The patient describes having numerous moles · a clinical photograph of a skin lesion · by self-report, a personal history of skin cancer, a family history of skin cancer, and a personal history of cancer · the patient says their skin reddens with sun exposure · a female patient age 54 · acquired for a research image collection, with no referral diagnosis — 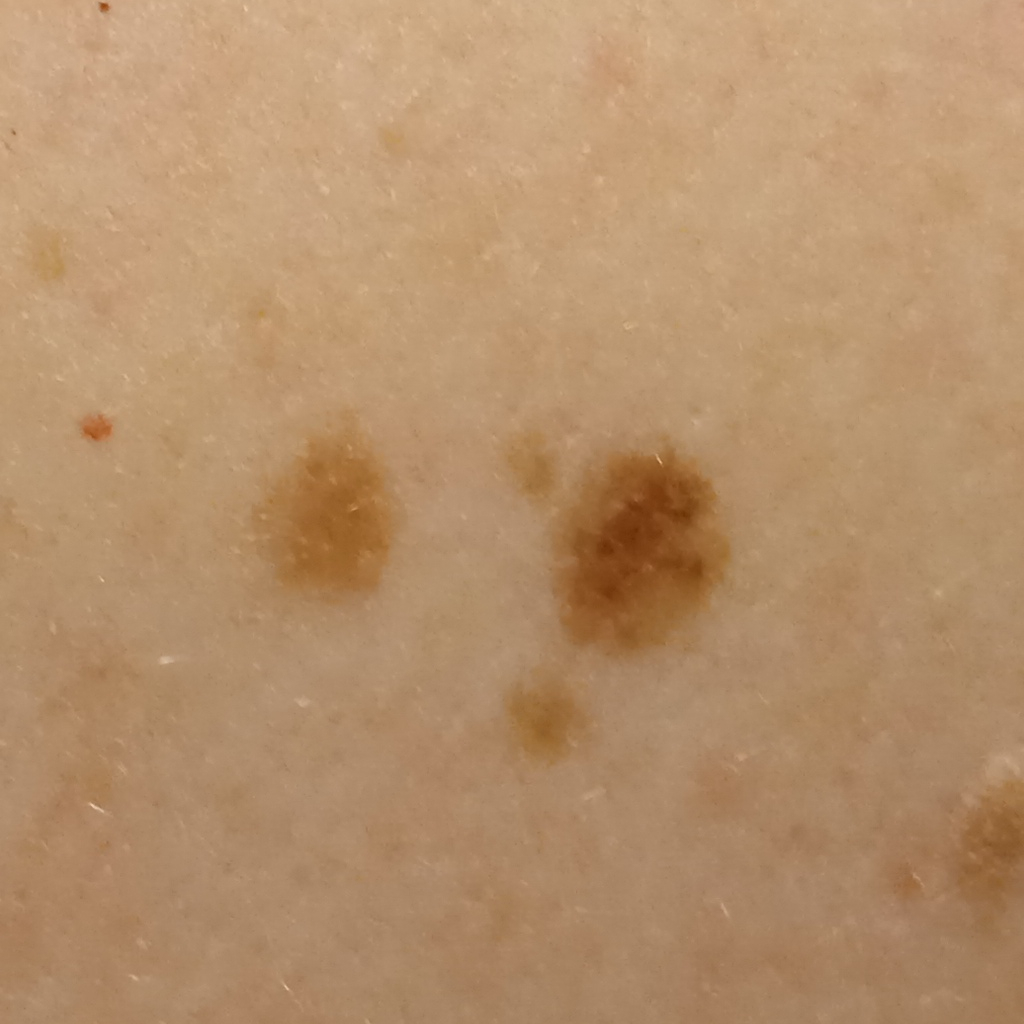site = the back; size = 6.4 mm; diagnosis = atypical (dysplastic) nevus — dermatologist consensus.